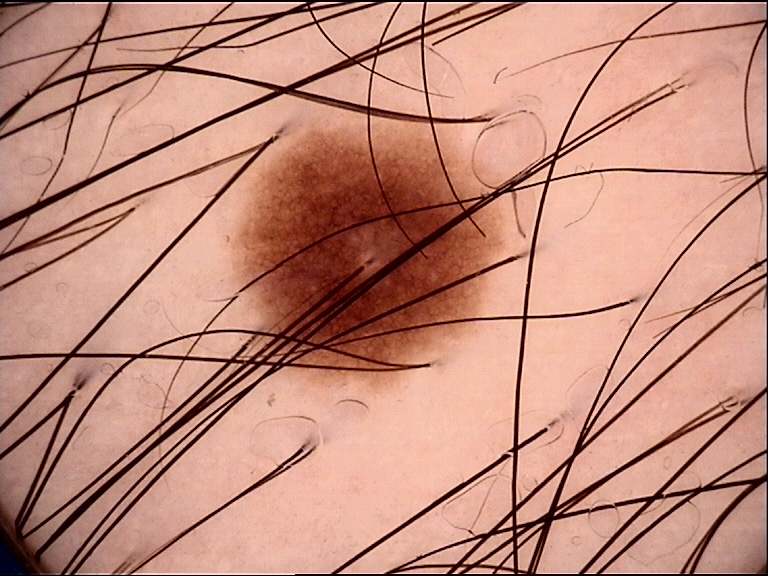Labeled as a junctional nevus.